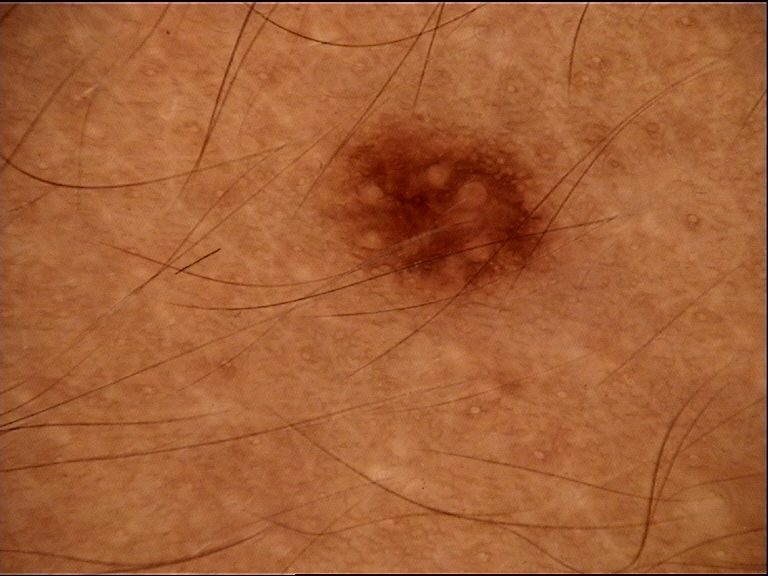Case:
– imaging — dermatoscopy
– diagnosis — dysplastic junctional nevus (expert consensus)